A male patient roughly 65 years of age; a dermoscopic image of a skin lesion: 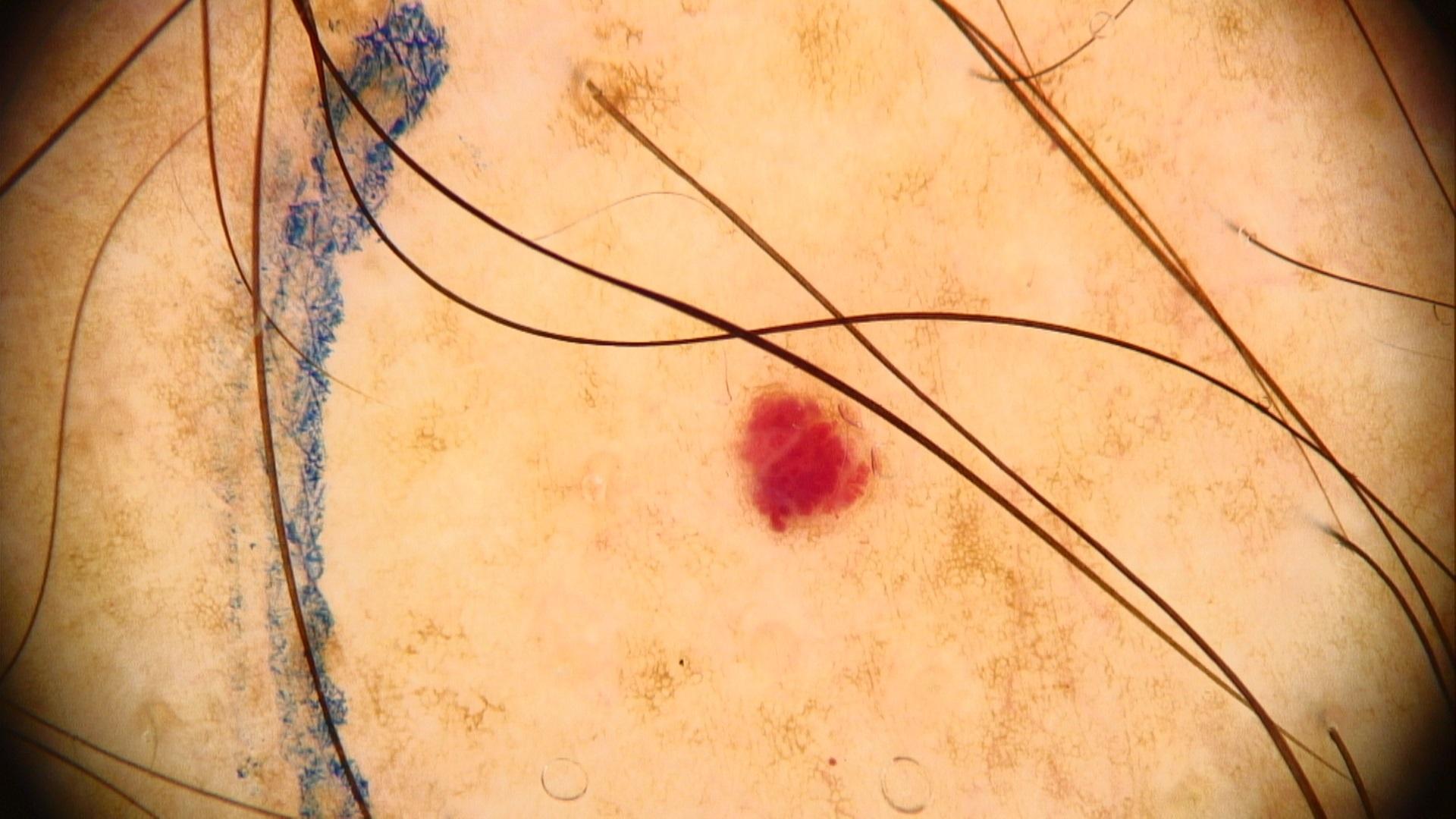The clinical impression was a vascular lesion.